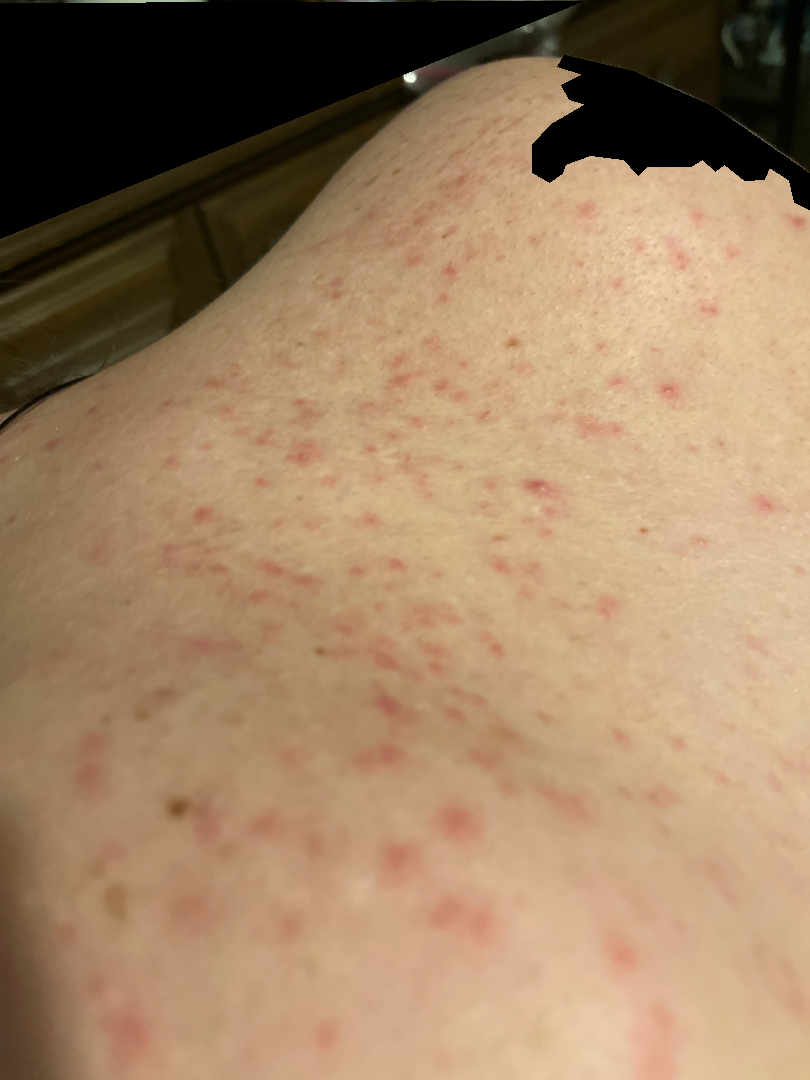Q: What is the differential diagnosis?
A: Folliculitis (1.00)